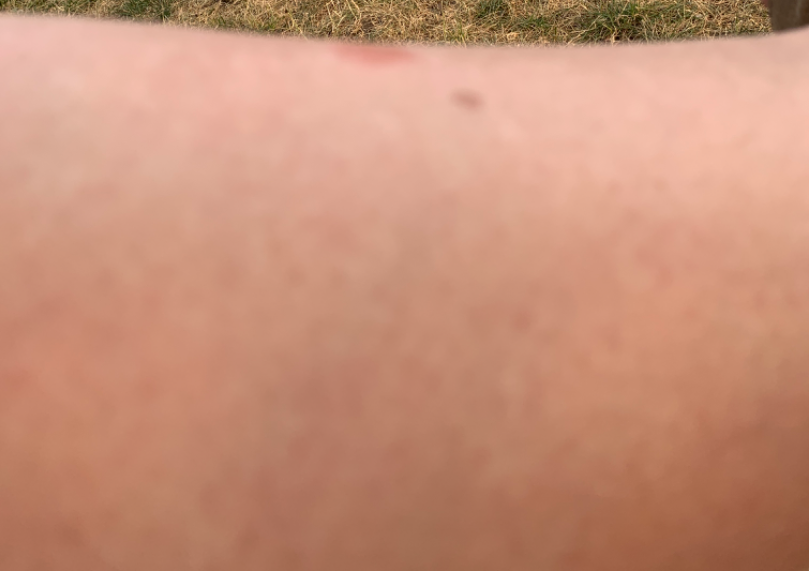Notes:
- assessment · ungradable on photographic review
- patient describes the issue as · a growth or mole
- patient · female, age 50–59
- systemic symptoms · joint pain and fatigue
- photo taken · at an angle
- present for · one to four weeks
- symptoms · none reported
- site · leg
- texture · flat and rough or flaky